The chart notes prior skin cancer (patient or family), tobacco use, alcohol use, prior malignancy (patient or family), and pesticide exposure. The patient was assessed as Fitzpatrick skin type III. A clinical photograph showing a skin lesion:
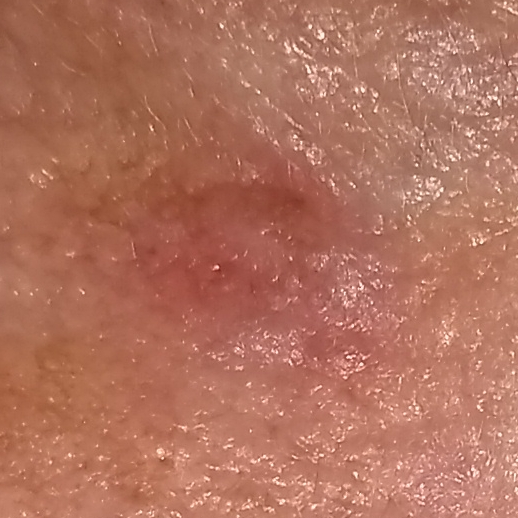– pathology · basal cell carcinoma (biopsy-proven)